Female contributor, age 18–29; a close-up photograph.
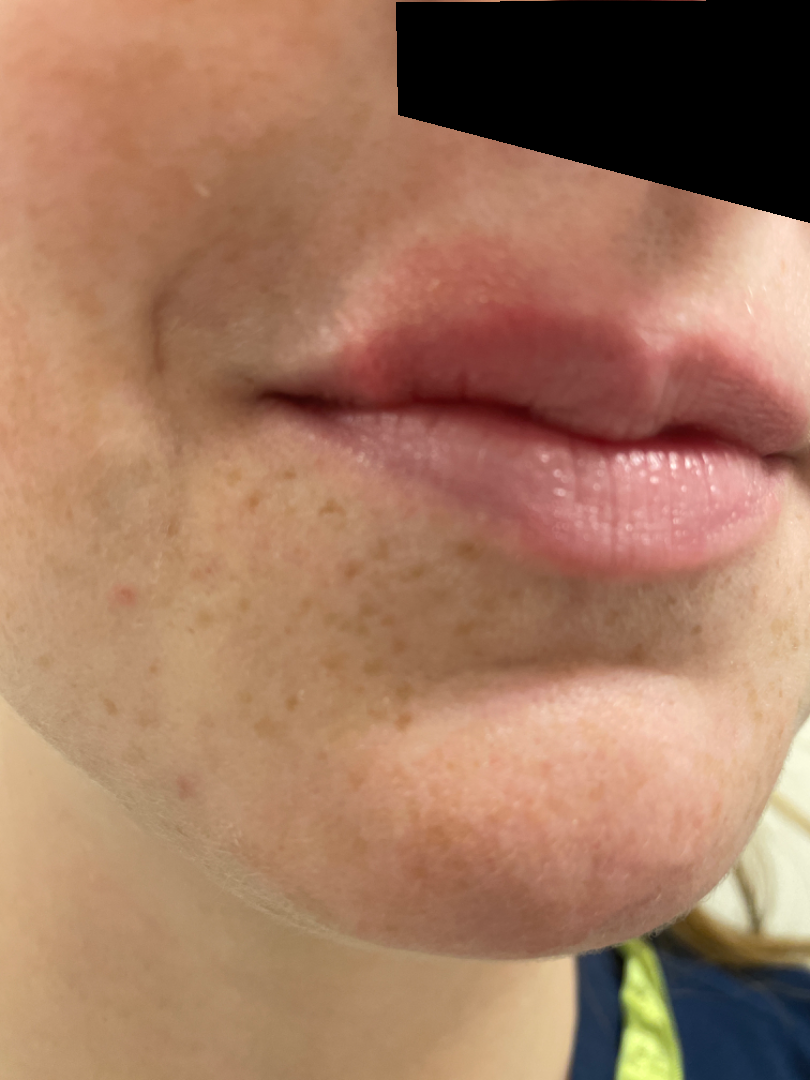Eczema and Irritant Contact Dermatitis were each considered, in no particular order; less probable is Herpes Simplex.